This is a close-up image · the back of the torso is involved — 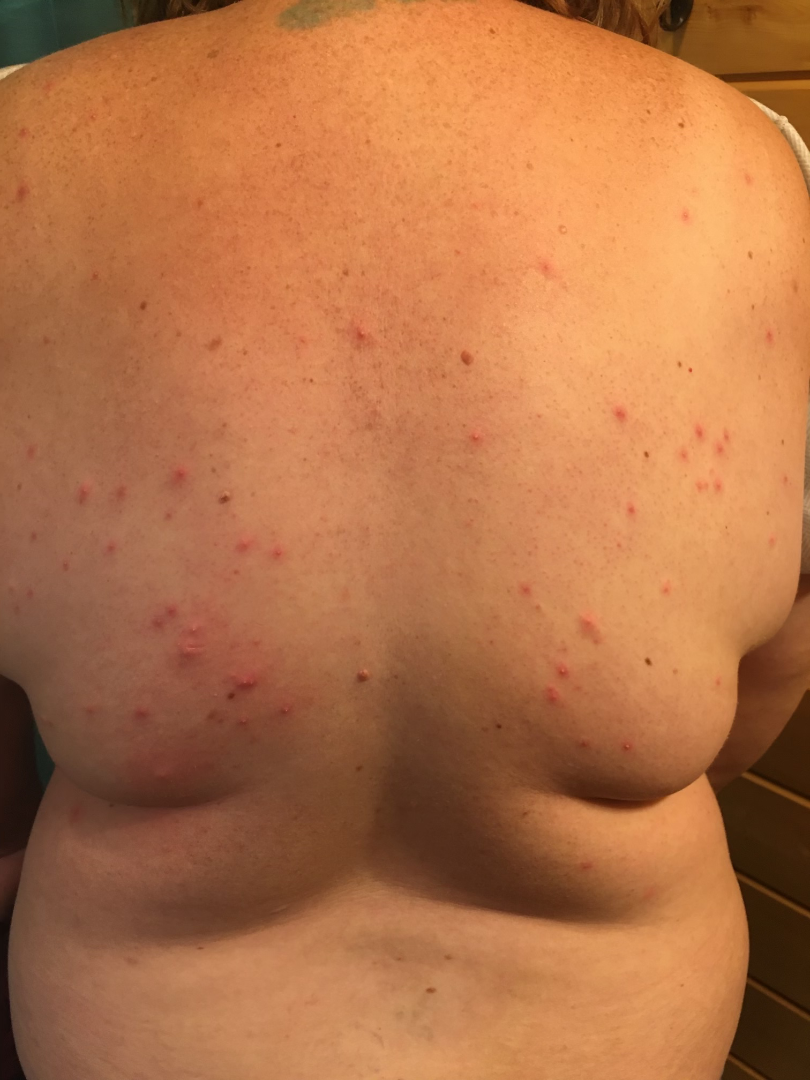Patient information: The patient indicates the lesion is raised or bumpy. The patient indicates the condition has been present for about one day. The lesion is associated with itching. Skin tone: lay graders estimated Monk skin tone scale 4 (US pool) or 3 (India pool). Self-categorized by the patient as acne. Review: On remote dermatologist review: Folliculitis (most likely).